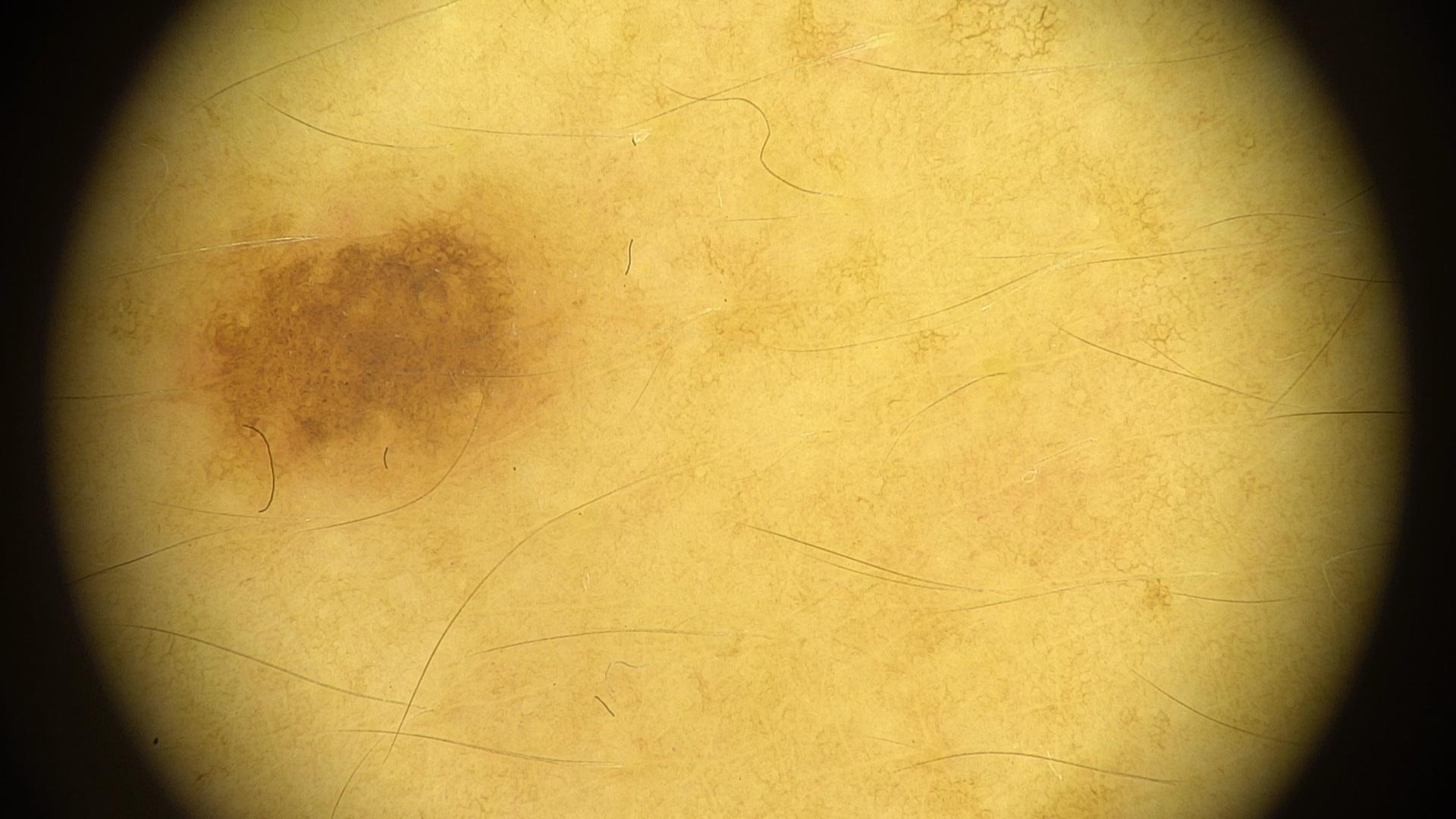{"diagnosis": {"name": "Nevus", "malignancy": "benign", "confirmation": "expert clinical impression", "lineage": "melanocytic"}}